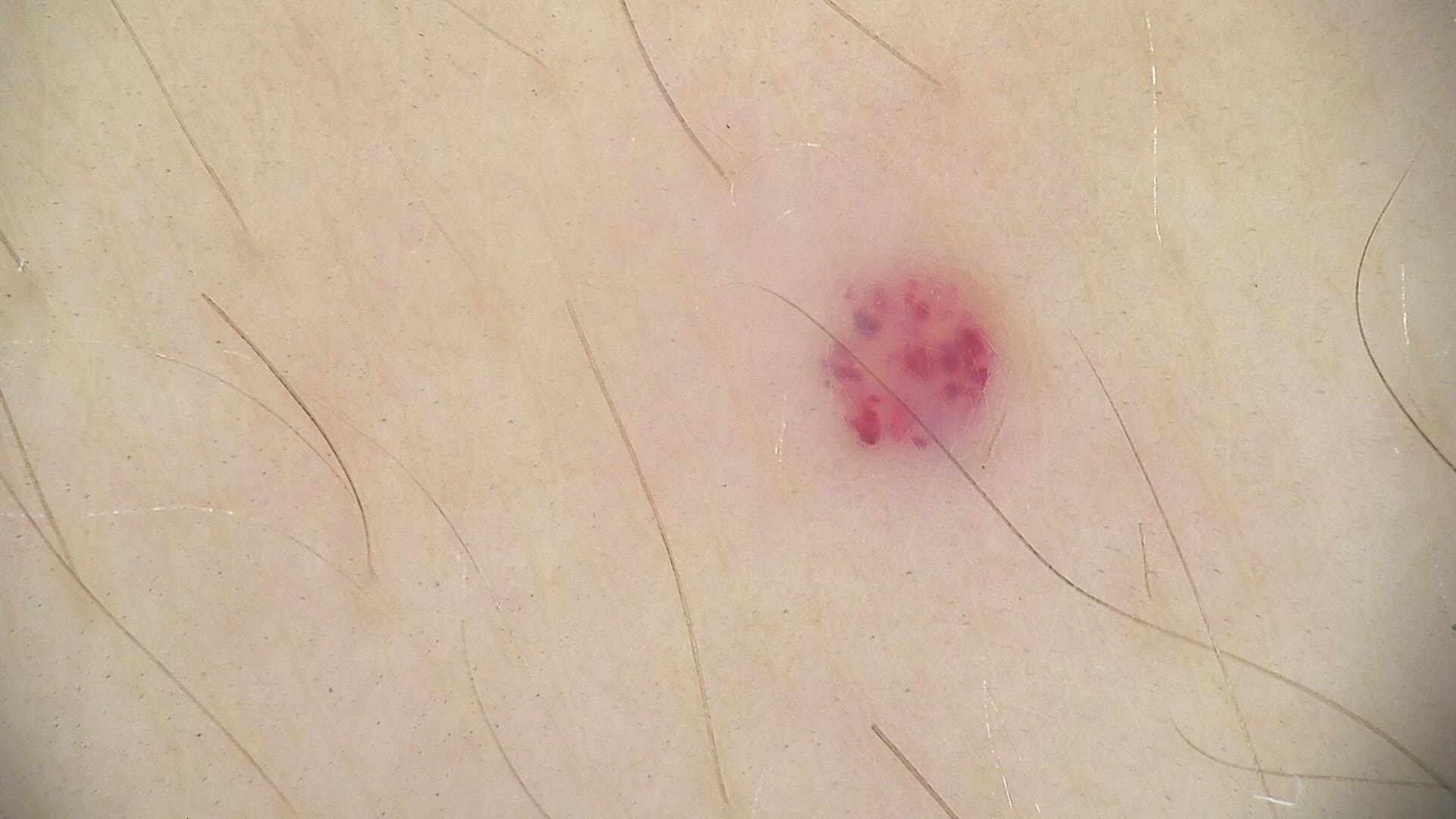Case:
- category: vascular
- assessment: hemangioma (expert consensus)